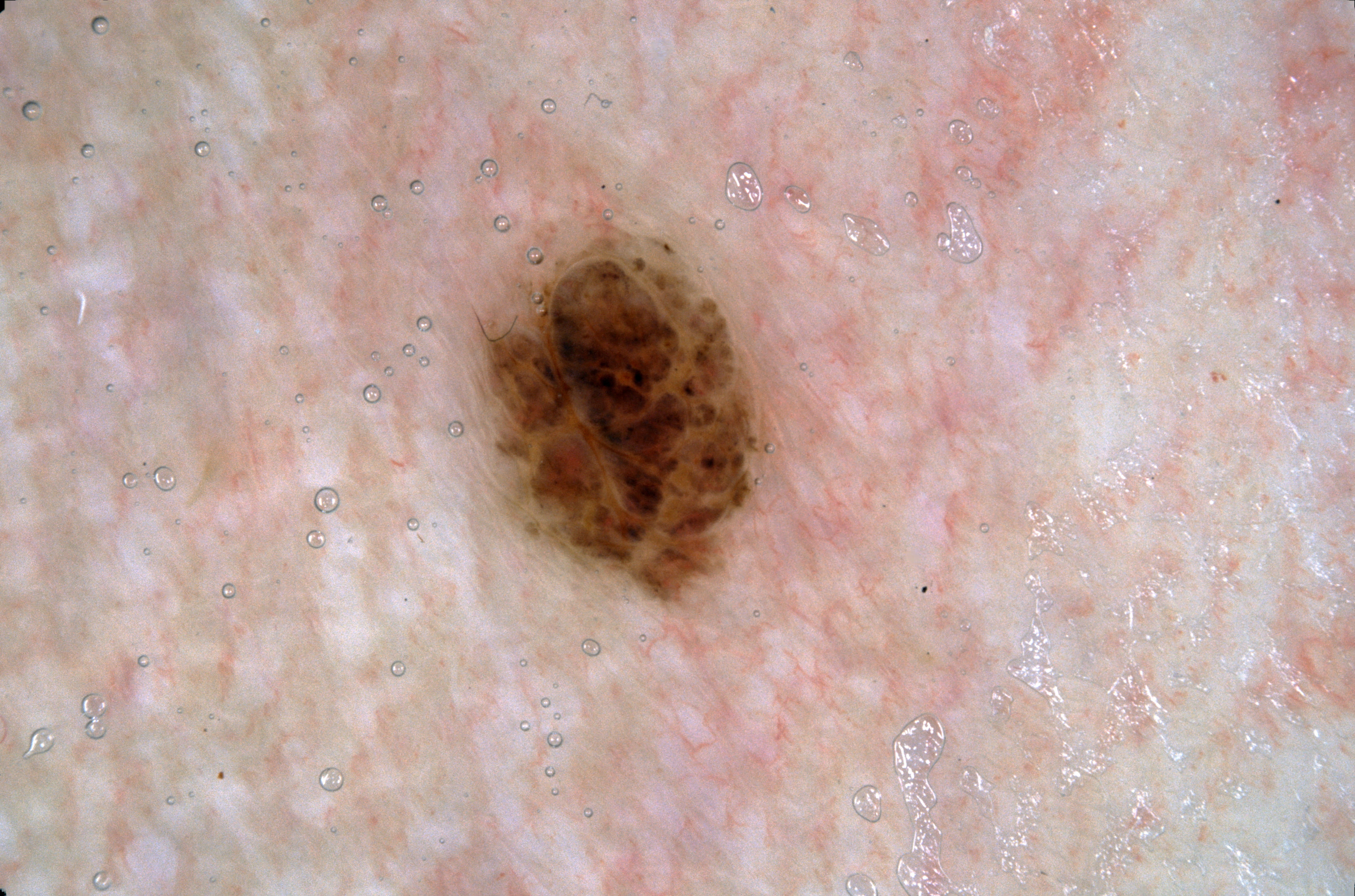- imaging: dermoscopic image
- patient: male, in their mid-20s
- dermoscopic features assessed but absent: pigment network, negative network, milia-like cysts, and streaks
- size: ~7% of the field
- lesion bbox: [469,205,783,611]
- diagnosis: a melanocytic nevus, a benign lesion